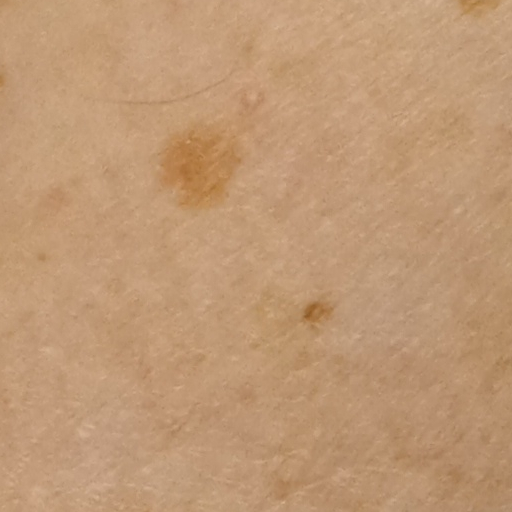Collected as part of a research study, without a referral diagnosis.
A clinical photograph showing a skin lesion.
A female subject 71 years of age.
The lesion is on an arm.
Dermatologist review favored a melanocytic nevus.